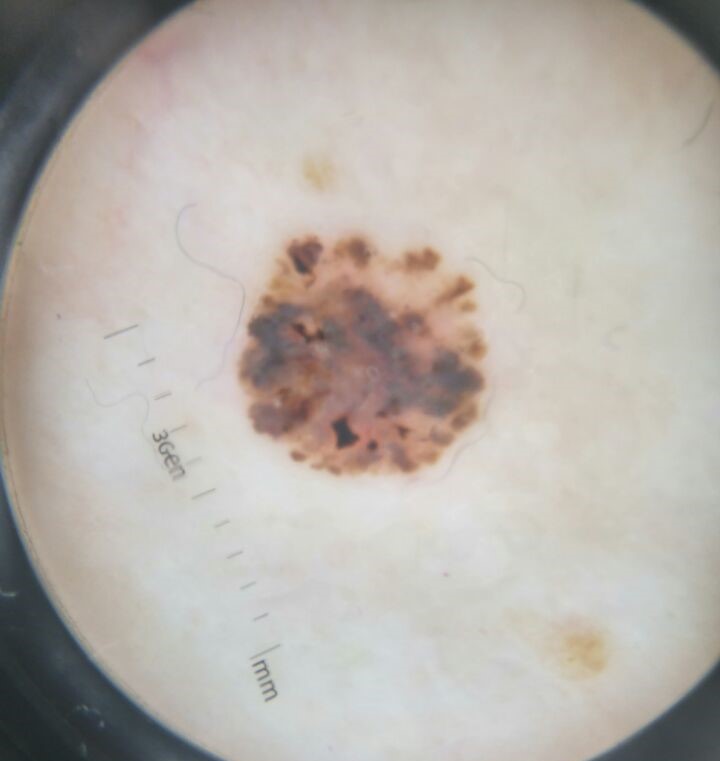Biopsy-confirmed as a keratinocytic, malignant lesion — a basal cell carcinoma.